Close-up view; located on the back of the hand and arm; male patient, age 30–39 — 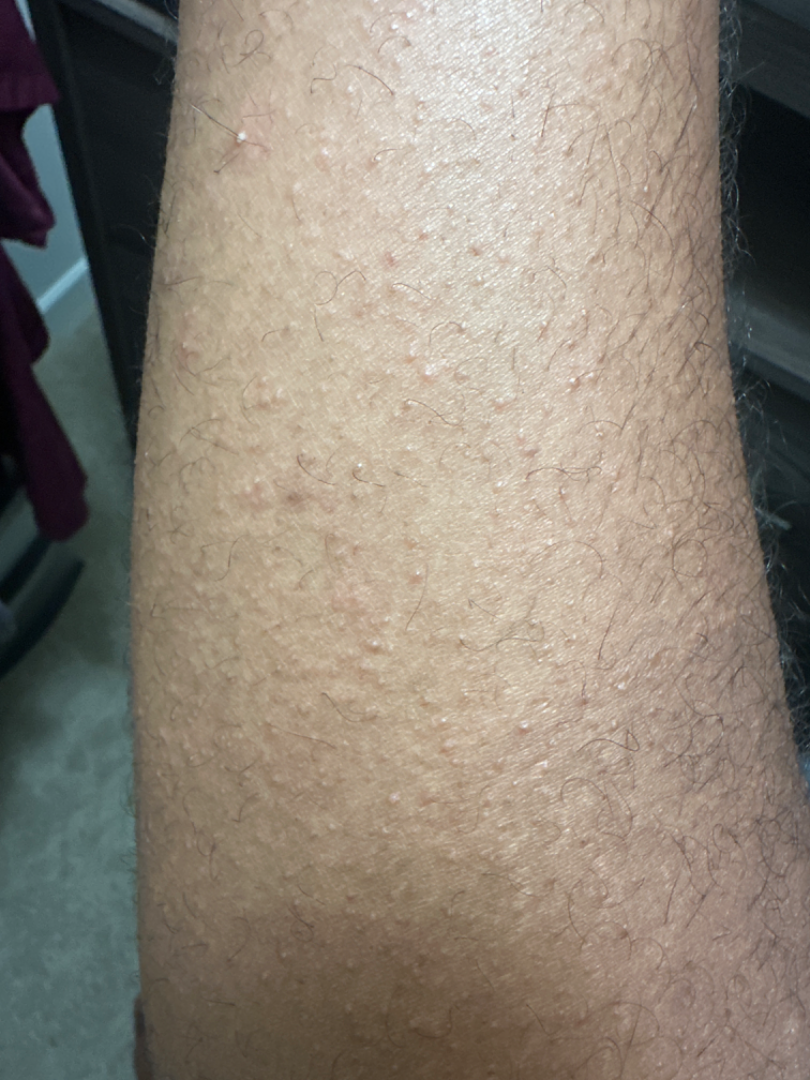differential:
  leading:
    - Keratosis pilaris
  considered:
    - Miliaria